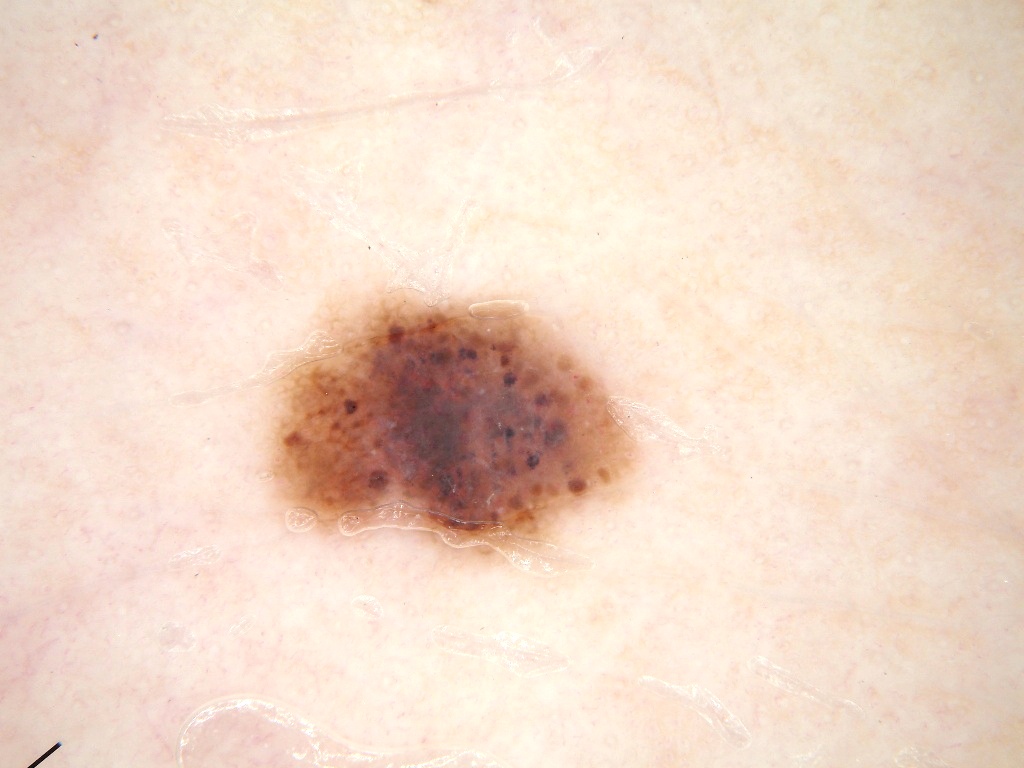Q: What kind of image is this?
A: dermoscopy of a skin lesion
Q: Patient demographics?
A: female, aged 23 to 27
Q: Which dermoscopic features were noted?
A: pigment network, milia-like cysts, and globules; absent: streaks and negative network
Q: What is the lesion's bounding box?
A: [270, 299, 630, 554]
Q: What is this lesion?
A: a melanocytic nevus